The photograph is a close-up of the affected area — 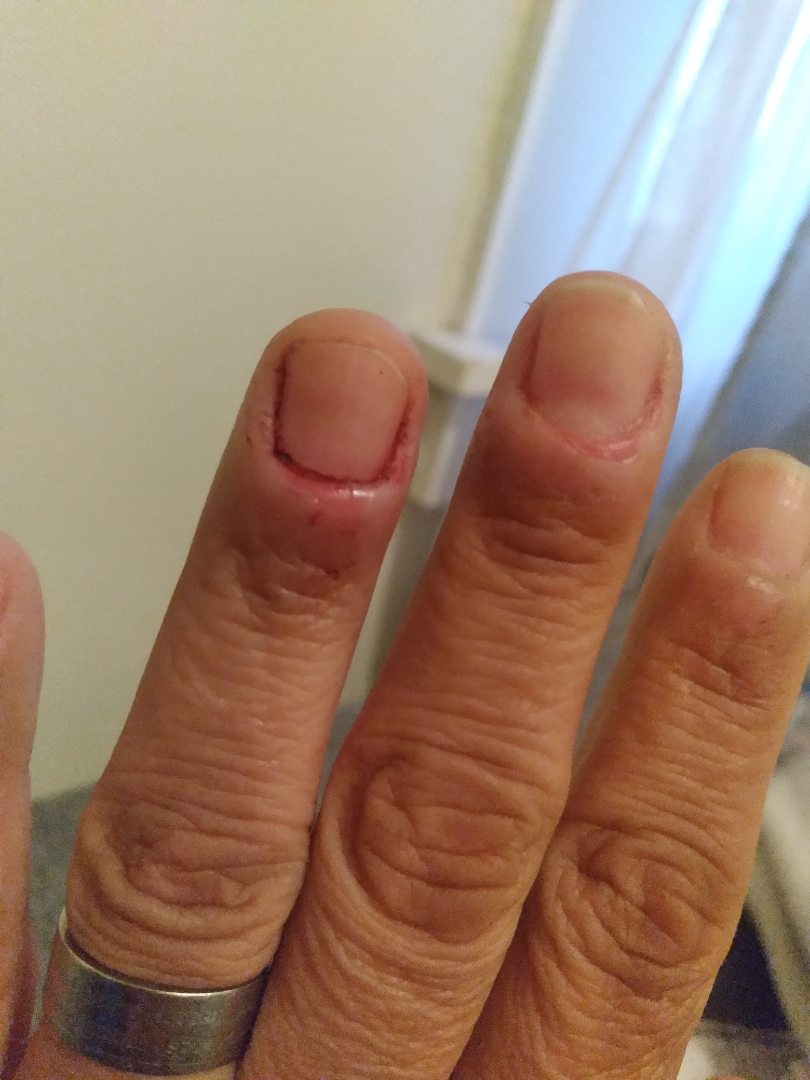The patient notes the lesion is fluid-filled. The lesion is associated with bleeding. No constitutional symptoms were reported. Reviewed remotely by one dermatologist: most consistent with Paronychia.